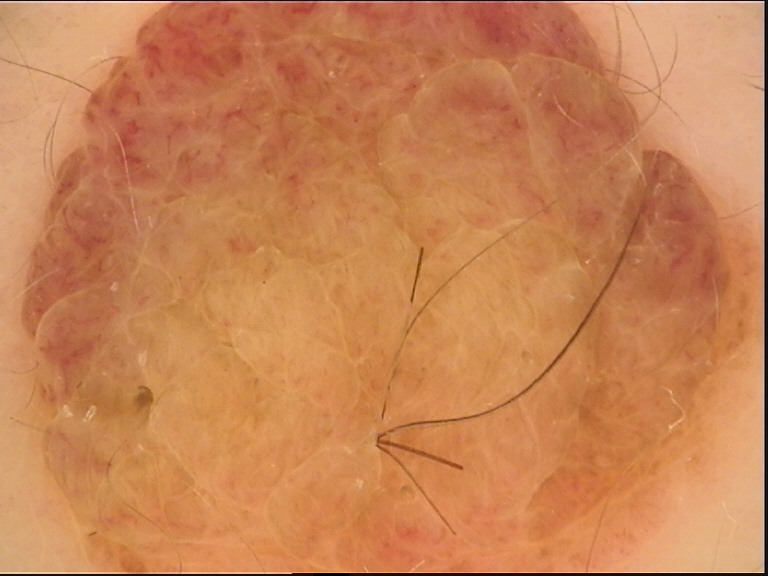Q: What was the diagnostic impression?
A: dermal nevus (expert consensus)